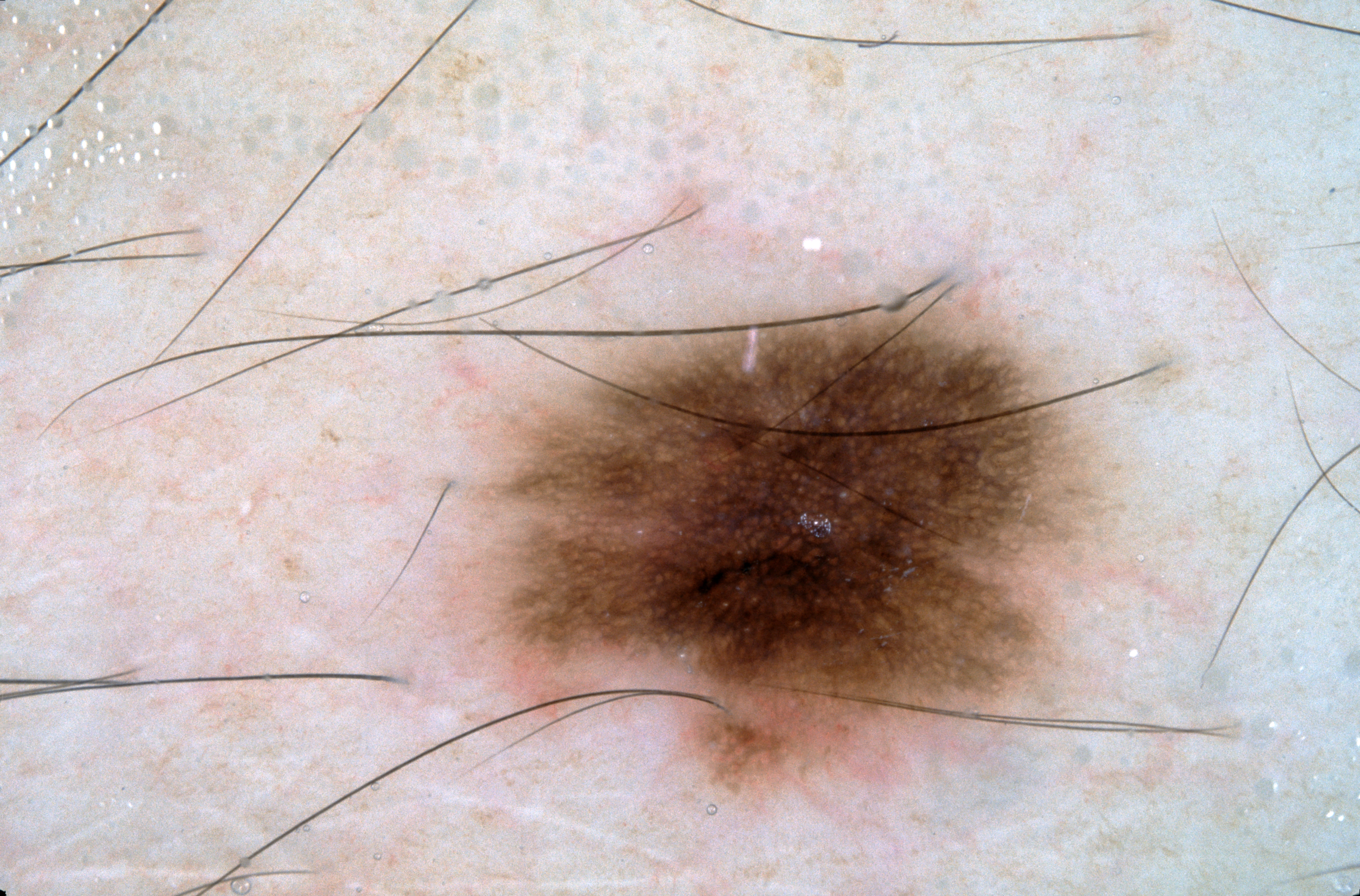This is a dermoscopic photograph of a skin lesion.
The subject is a male aged 38-42.
The lesion is located at <box>478, 294, 1105, 791</box>.
Dermoscopic assessment notes milia-like cysts and pigment network.
Consistent with a melanocytic nevus.